This image was taken at a distance. Female patient, age 18–29. Self-categorized by the patient as a rash. The patient also reports mouth sores. The patient notes the condition has been present for about one day. Symptoms reported: itching and bothersome appearance. The head or neck is involved: 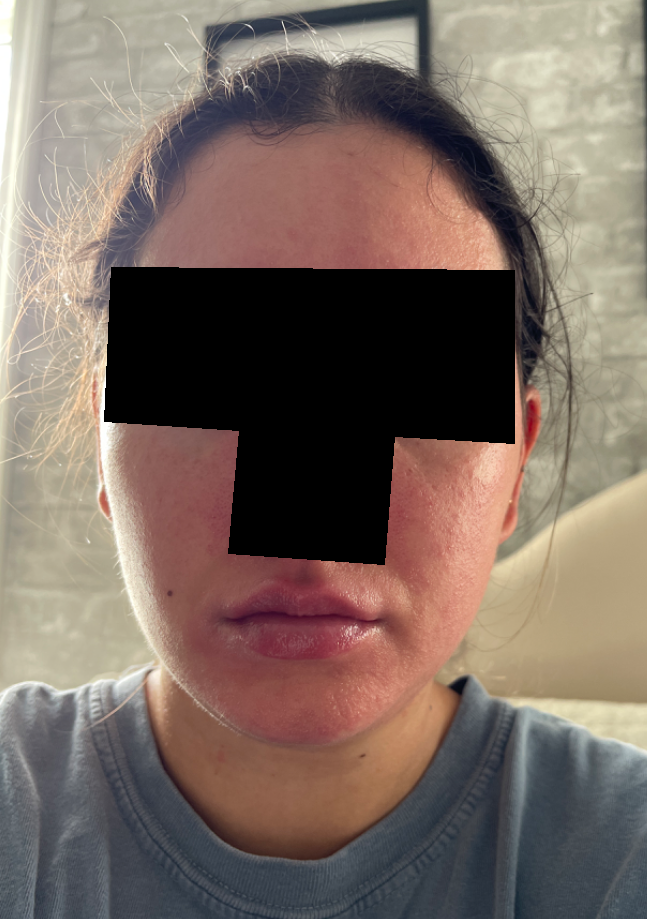Three independent reviewers: favoring Allergic Contact Dermatitis; a more distant consideration is Eczema; lower on the differential is Keratosis pilaris; less likely is Acne; less probable is Rosacea.